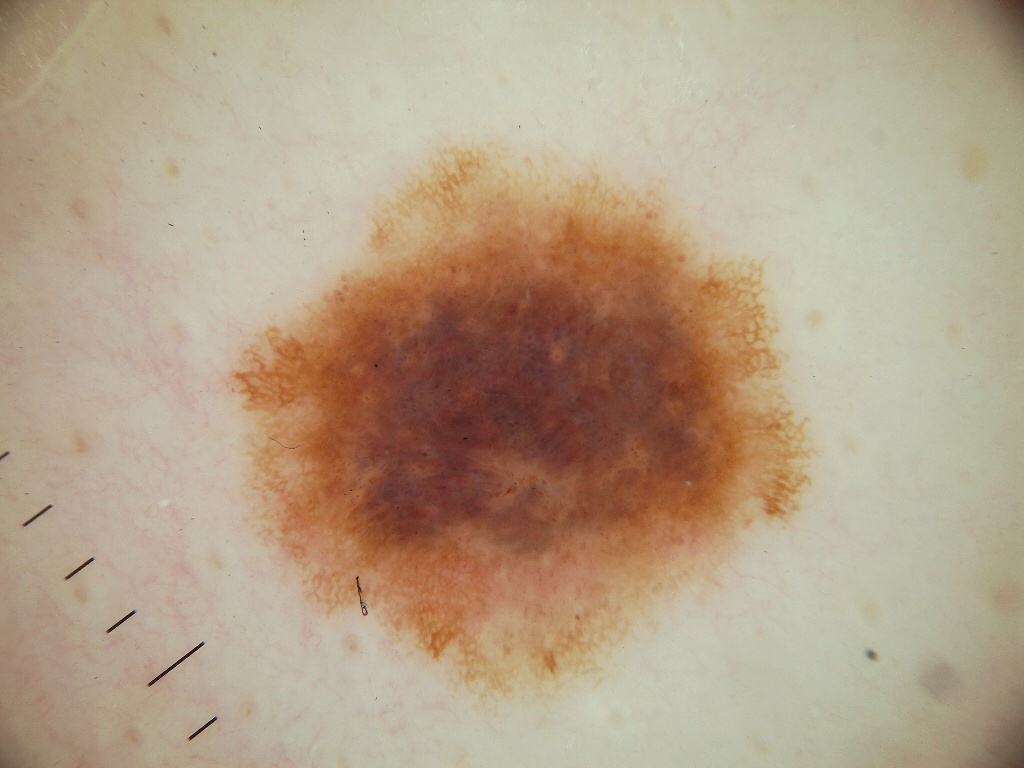  image:
    modality: dermoscopy
  lesion_extent: moderate
  dermoscopic_features:
    present:
      - pigment network
      - globules
    absent:
      - streaks
      - negative network
      - milia-like cysts
  lesion_location:
    bbox_xyxy:
      - 221
      - 143
      - 814
      - 701
  diagnosis:
    name: melanoma
    malignancy: malignant
    lineage: melanocytic
    provenance: histopathology